A dermoscopic view of a skin lesion — 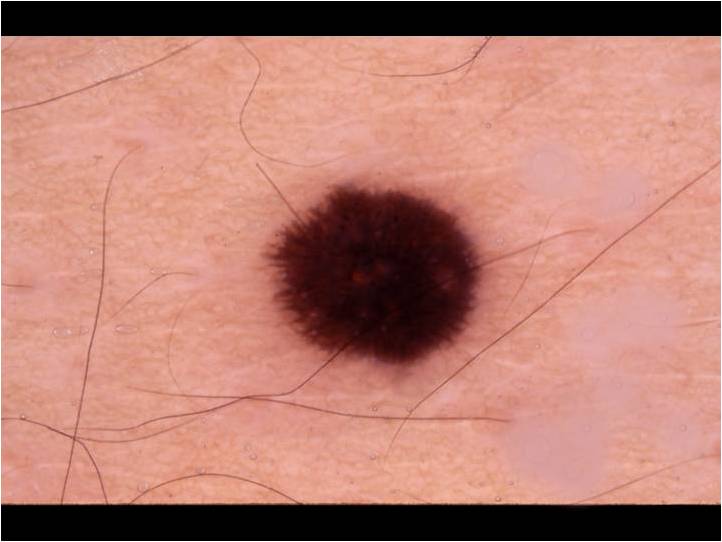lesion bbox — x1=255 y1=181 x2=484 y2=369
impression — a benign skin lesion